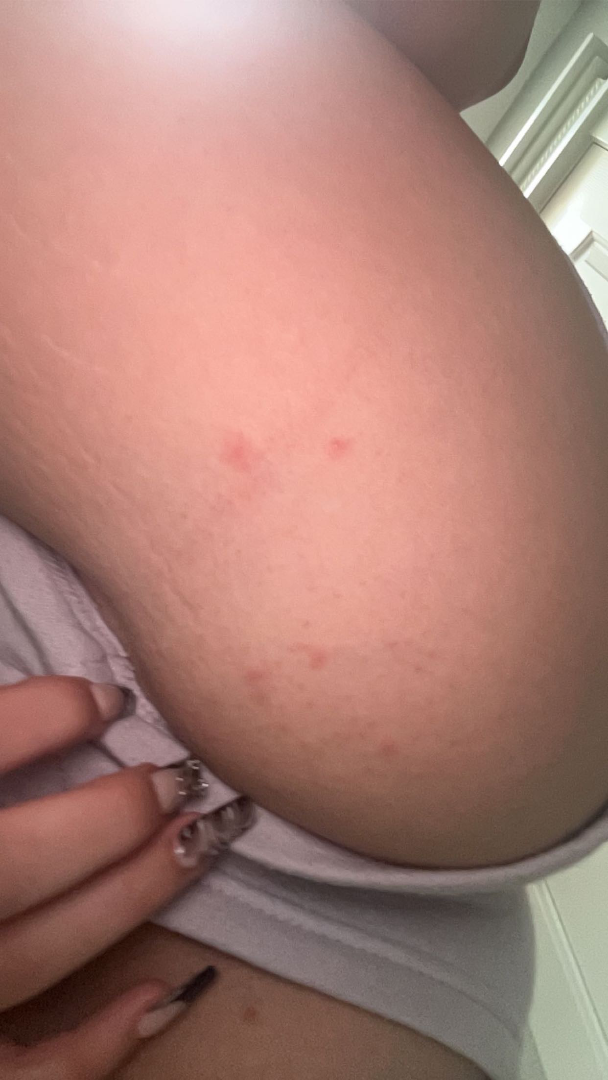assessment — ungradable on photographic review | image framing — close-up.